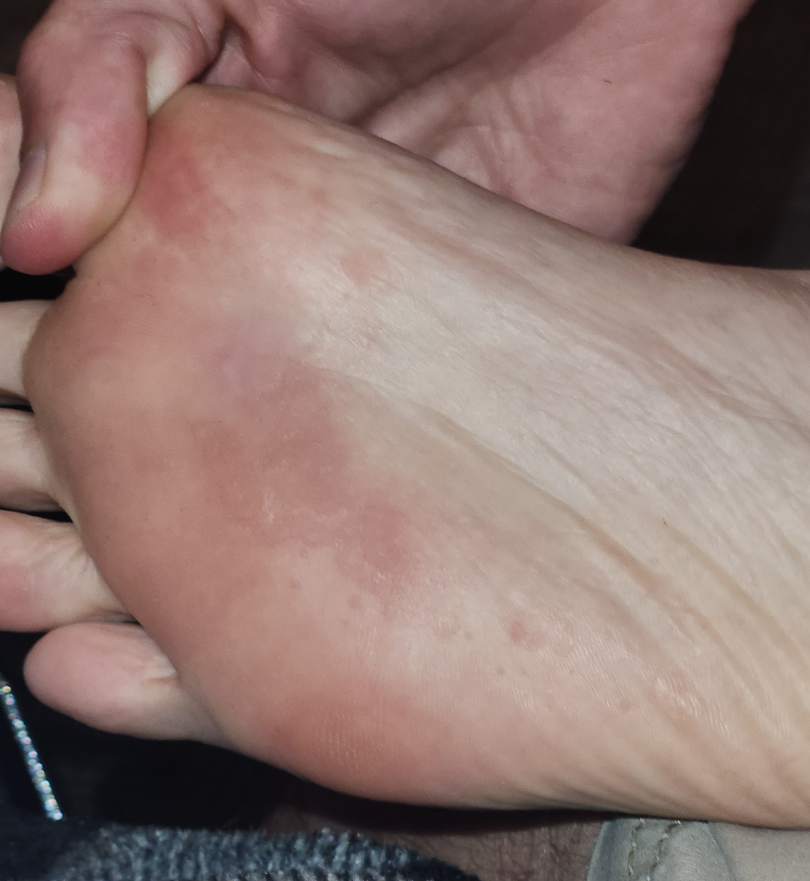{
  "assessment": "ungradable on photographic review",
  "body_site": "sole of the foot",
  "shot_type": "at a distance"
}